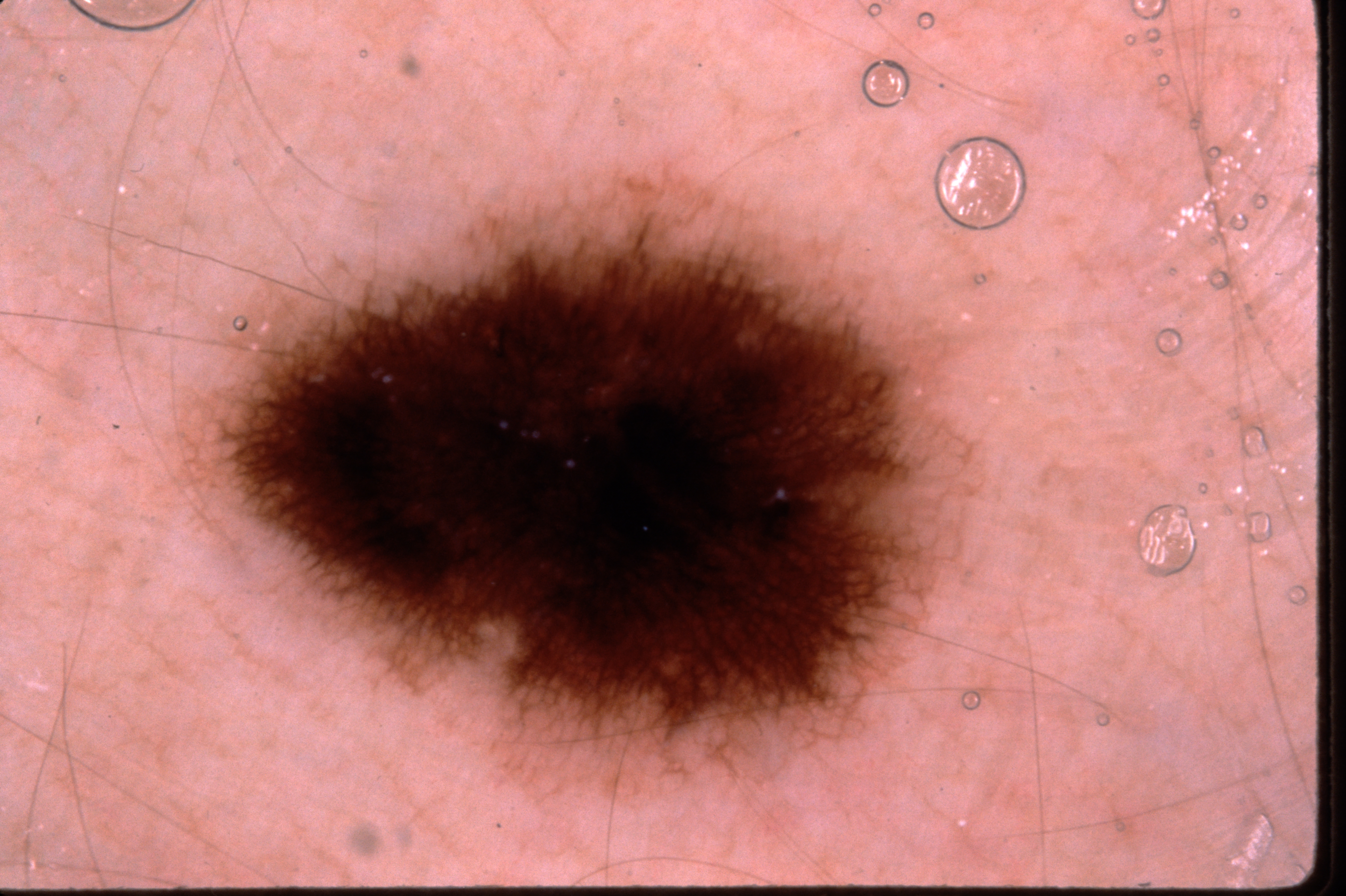A skin lesion imaged with a dermatoscope.
The subject is a female aged 23 to 27.
A moderately sized lesion.
Dermoscopy demonstrates pigment network, with no streaks, milia-like cysts, or negative network.
The lesion spans left=172, top=174, right=981, bottom=814.
The diagnostic assessment was a melanocytic nevus, a benign lesion.